A skin lesion imaged with a dermatoscope. The patient is FST II. A male subject aged 68-72 — 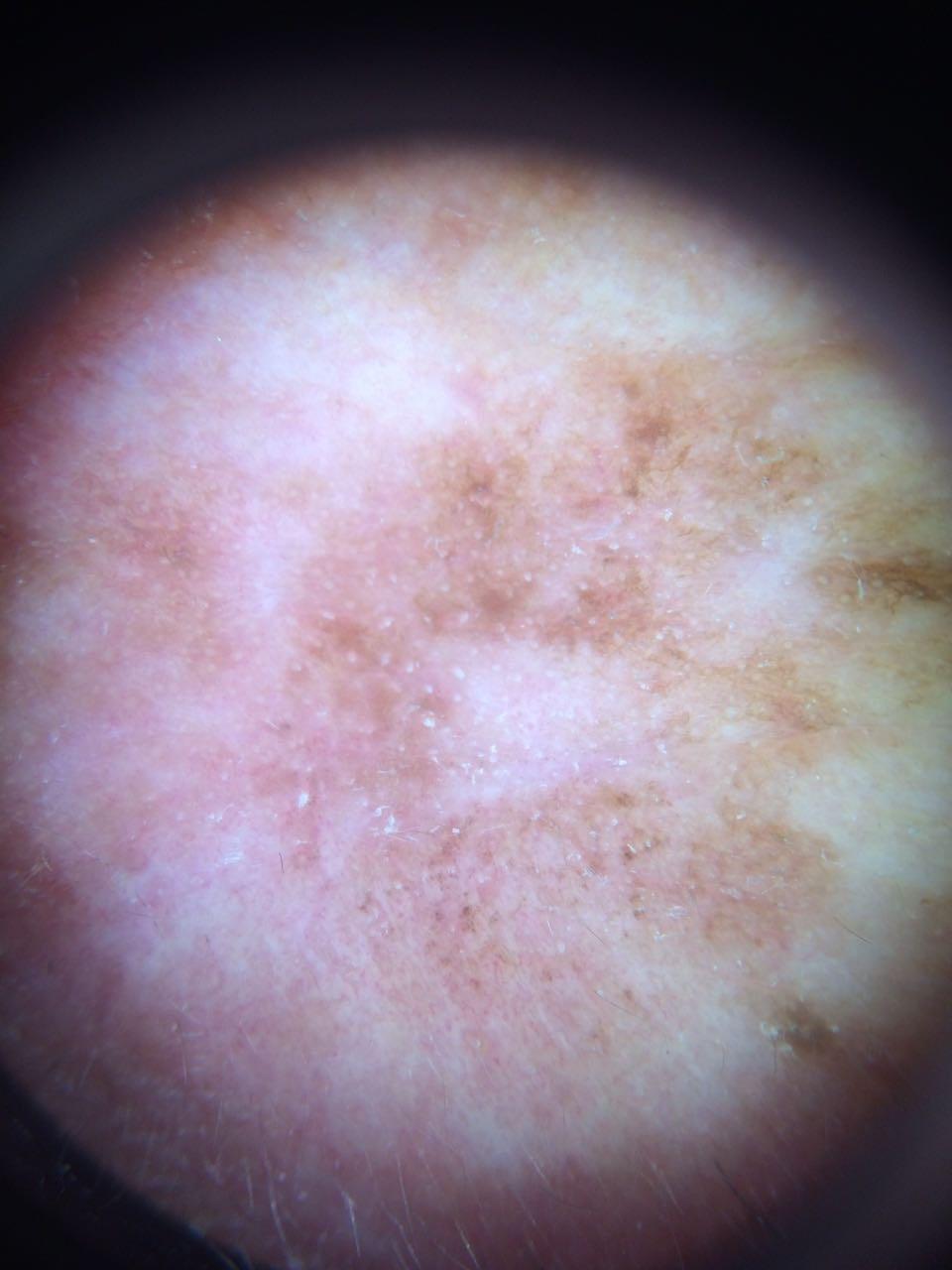  lesion_location:
    region: the head or neck
  diagnosis:
    name: Melanoma
    malignancy: malignant
    confirmation: histopathology